The lesion involves the head or neck; the photograph was taken at a distance.
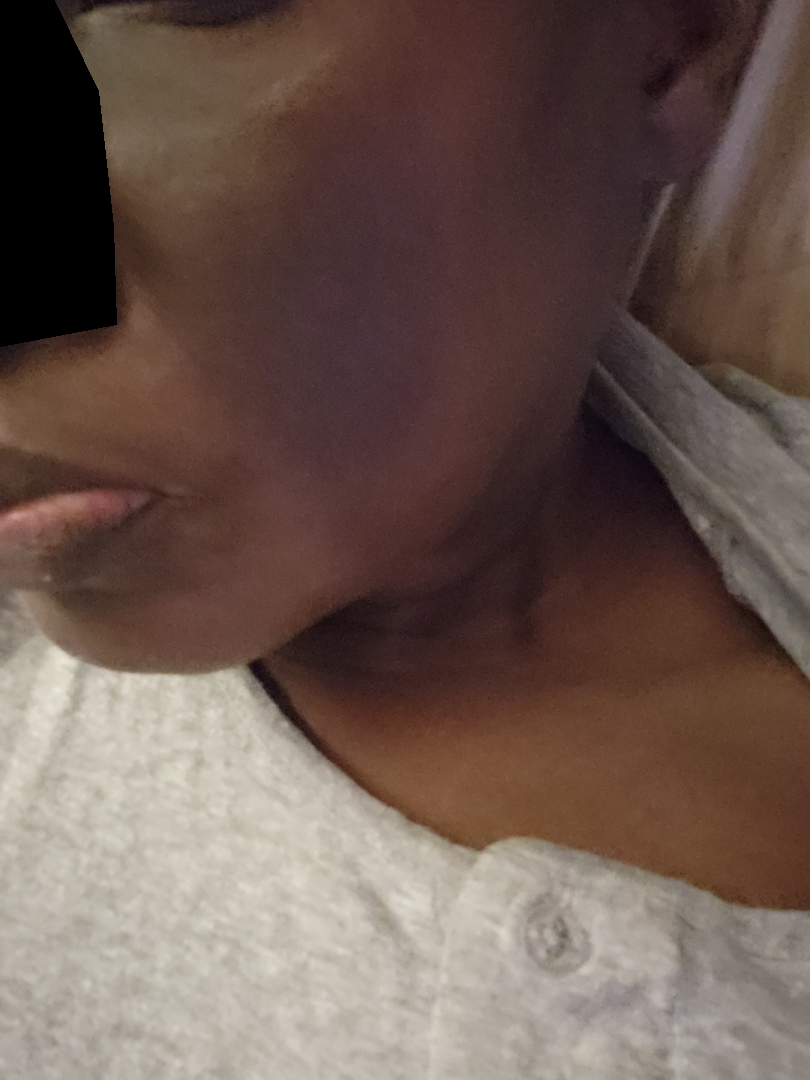On teledermatology review, Post-Inflammatory hyperpigmentation (leading); Melasma (possible); Drug induced abnormal pigmentation of skin (possible).